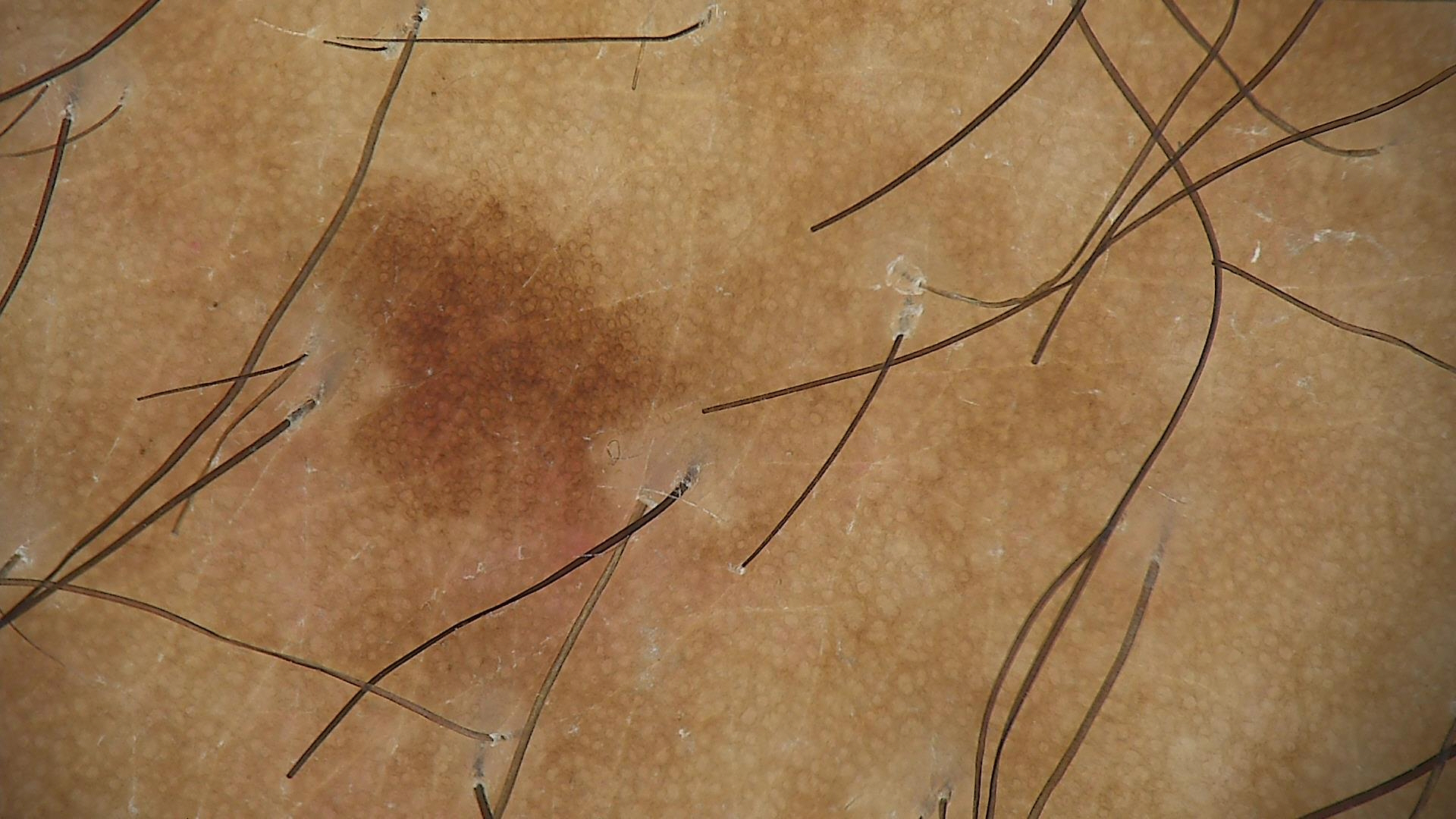image type = dermatoscopy | diagnostic label = solar lentigo (expert consensus).